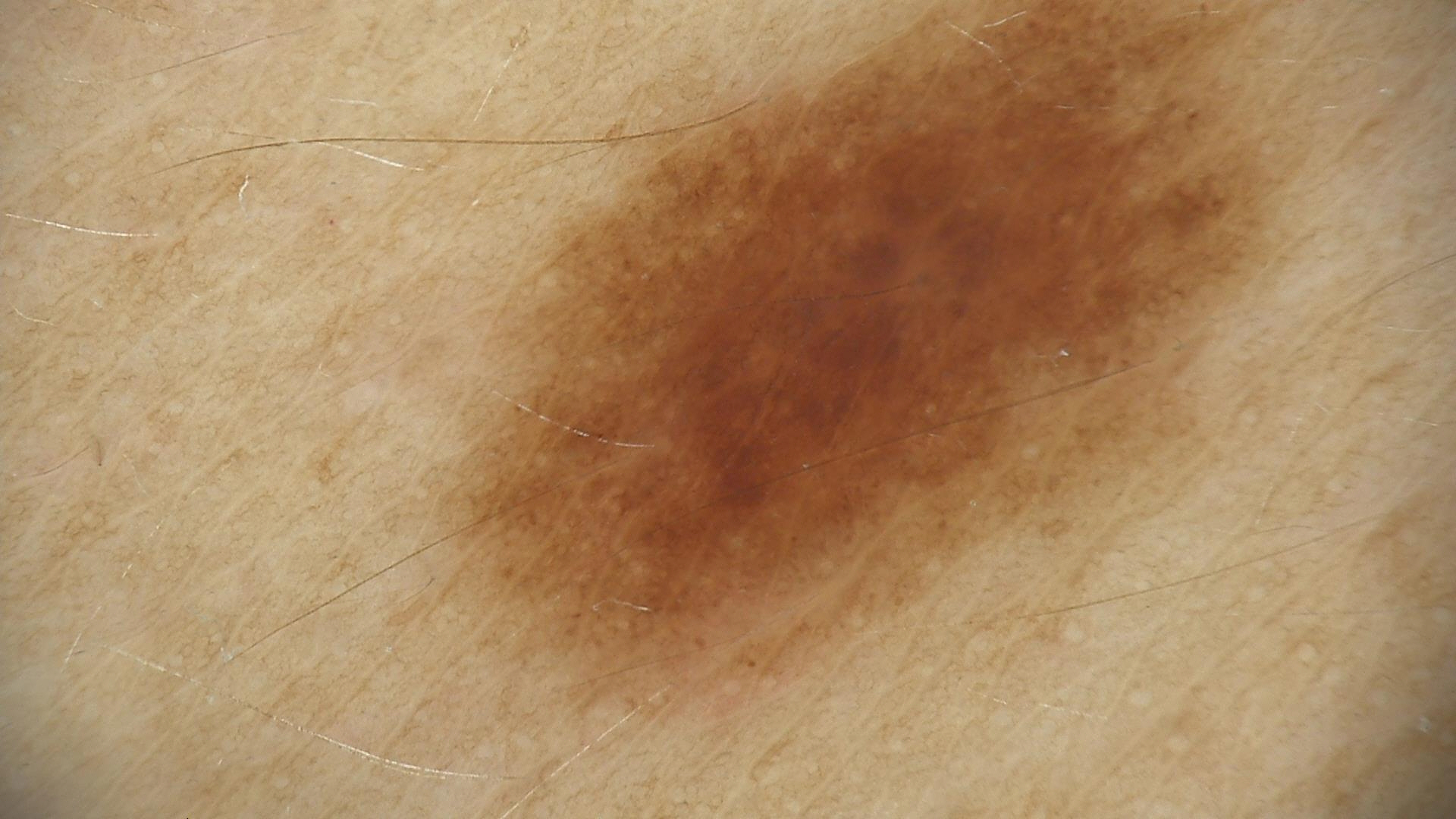diagnosis: dysplastic junctional nevus (expert consensus).